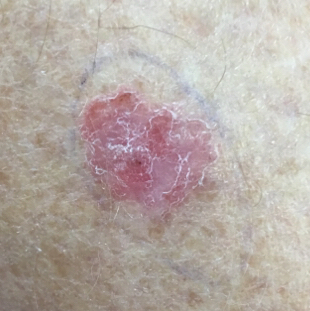Findings:
The patient was assessed as Fitzpatrick I. By history, prior skin cancer (patient or family). A clinical photo of a skin lesion taken with a smartphone. A female patient in their 80s. The lesion is on a thigh. Measuring about 15 × 12 mm.
Diagnosis:
Histopathology confirmed a squamous cell carcinoma.